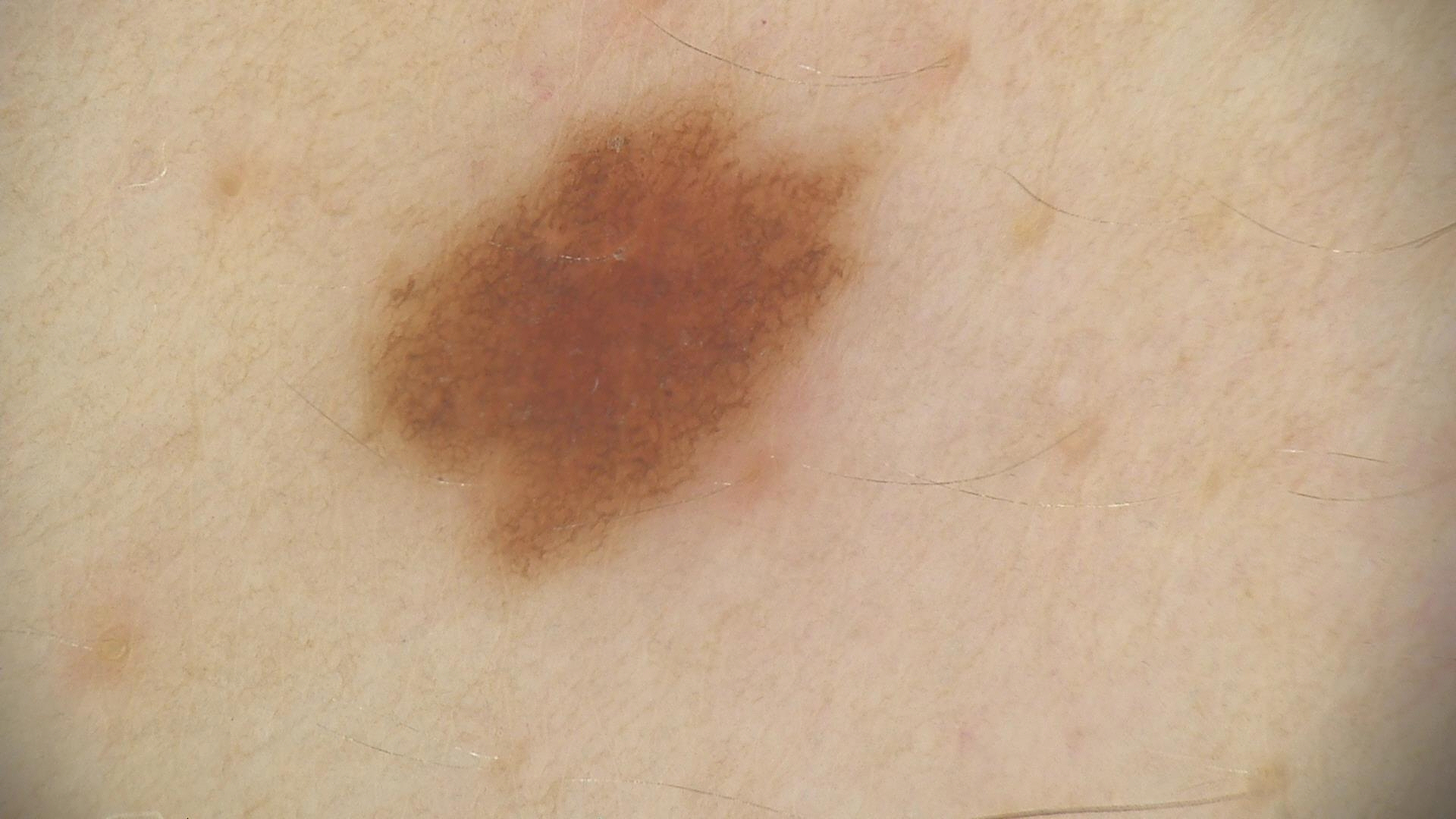Diagnosed as a dysplastic junctional nevus.